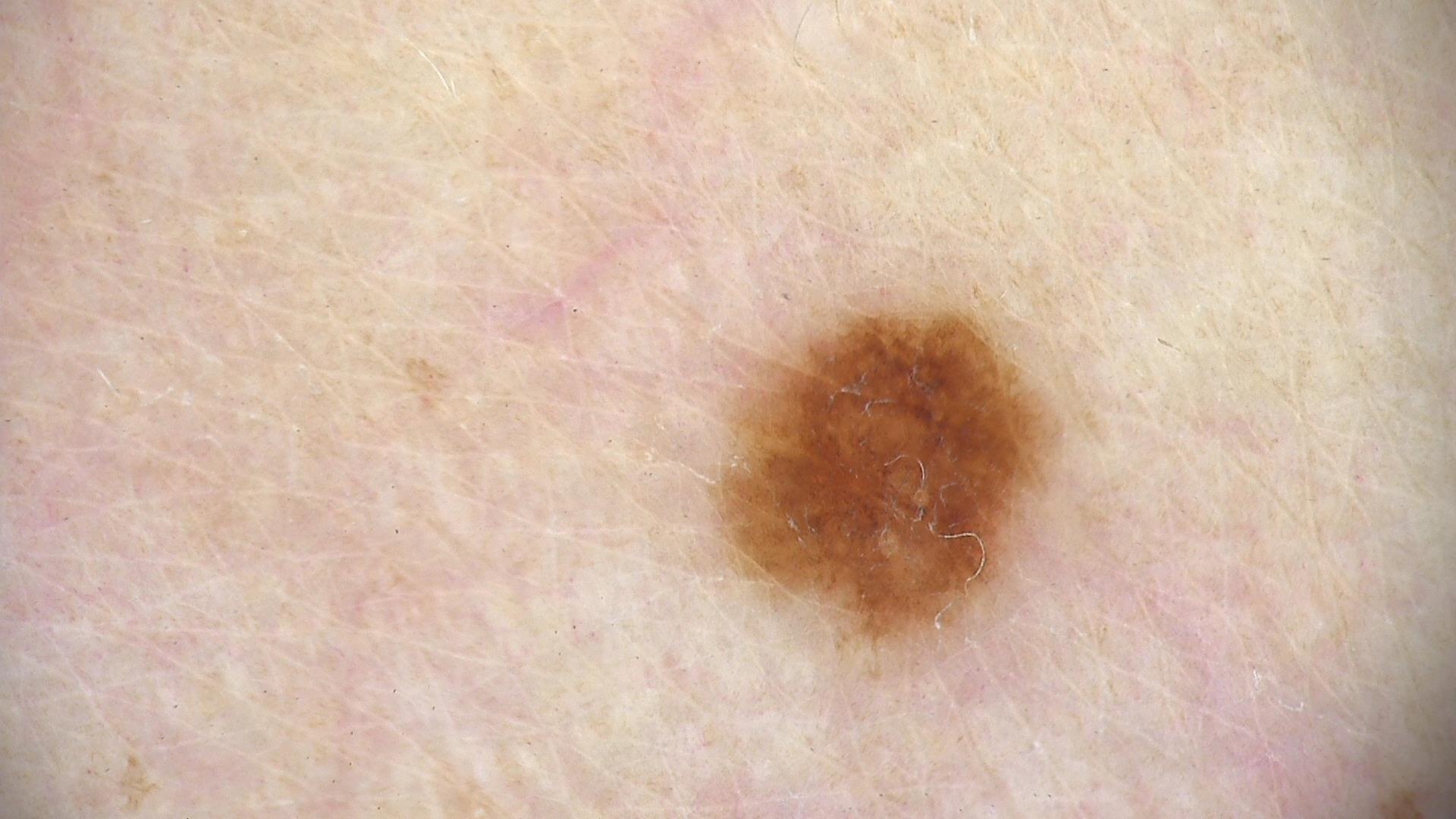Findings: A dermatoscopic image of a skin lesion. Conclusion: The diagnostic label was a banal lesion — a junctional nevus.